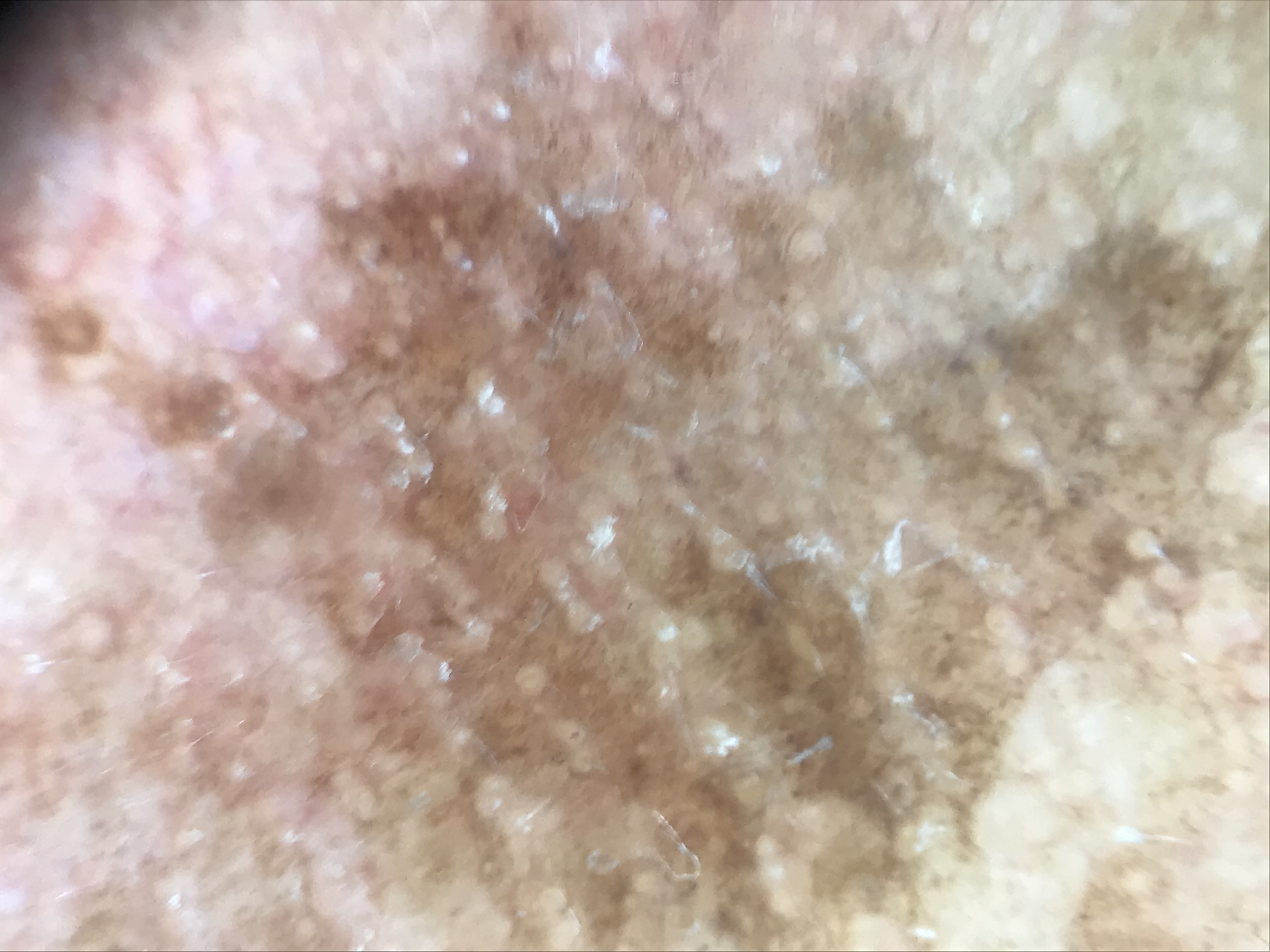assessment=actinic keratosis (expert consensus).